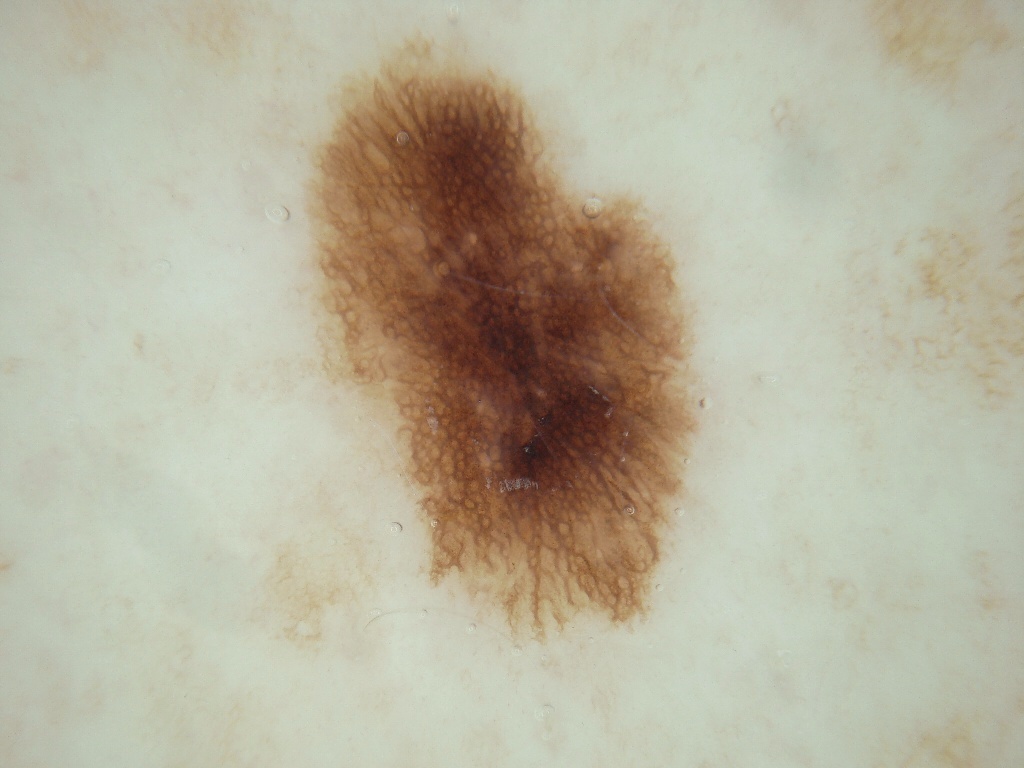This is a dermoscopic photograph of a skin lesion. The lesion takes up about 20% of the image. As (left, top, right, bottom), the lesion occupies the region 304/36/701/635. Clinically diagnosed as a benign lesion.